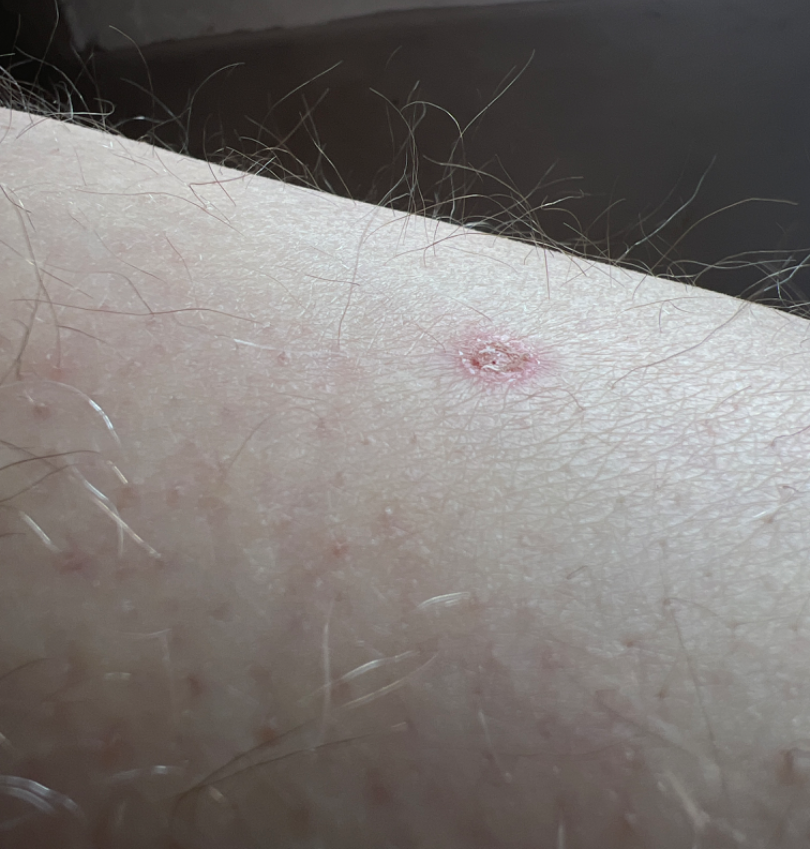The lesion involves the leg. The contributor is a male aged 60–69. An image taken at an angle. Basal Cell Carcinoma, SCC/SCCIS, Skin cancer, Psoriasis and Inflicted skin lesions were considered with similar weight; a remote consideration is Eczema.